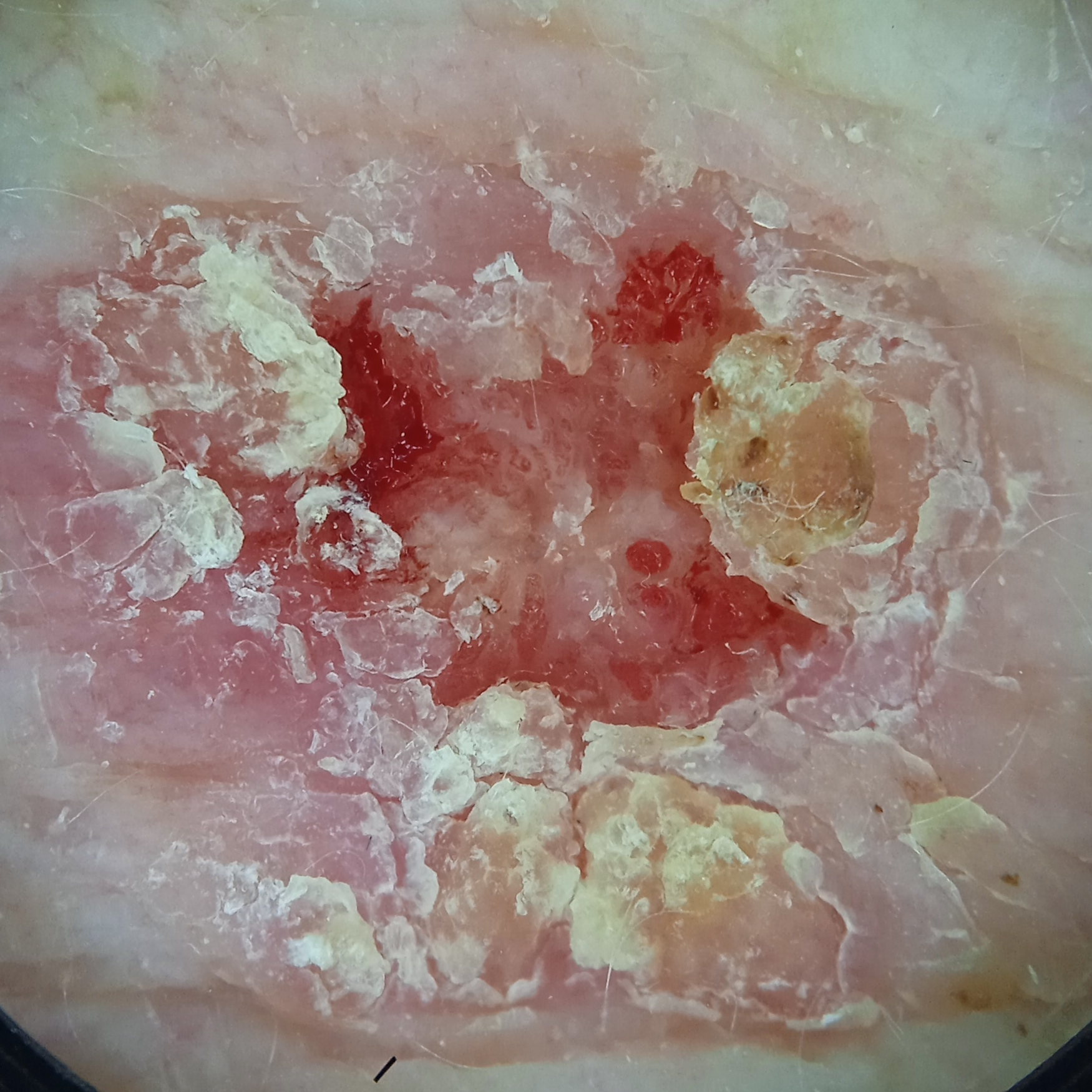{
  "diagnosis": {
    "name": "squamous cell carcinoma",
    "malignancy": "malignant"
  }
}